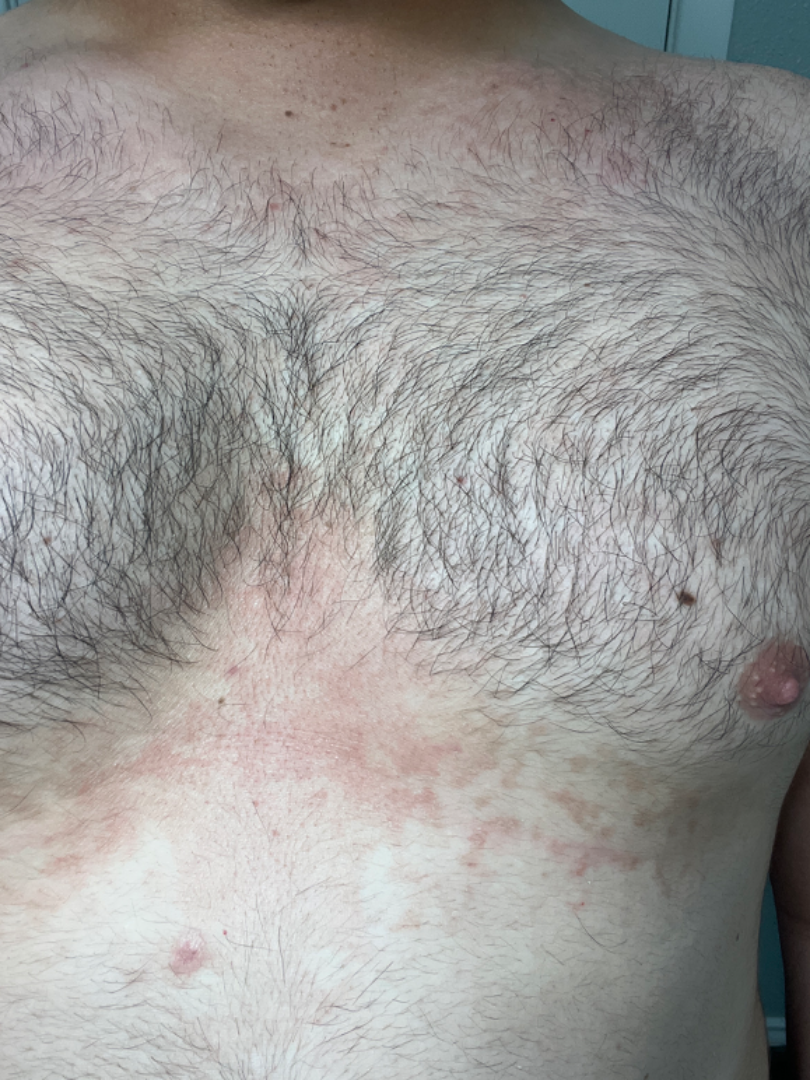| feature | finding |
|---|---|
| symptoms | enlargement, bothersome appearance and itching |
| duration | more than five years |
| lesion texture | flat and rough or flaky |
| constitutional symptoms | fatigue |
| shot type | close-up |
| subject | male, age 30–39 |
| differential | the reviewer's impression was Confluent and reticulate papillomatosis |